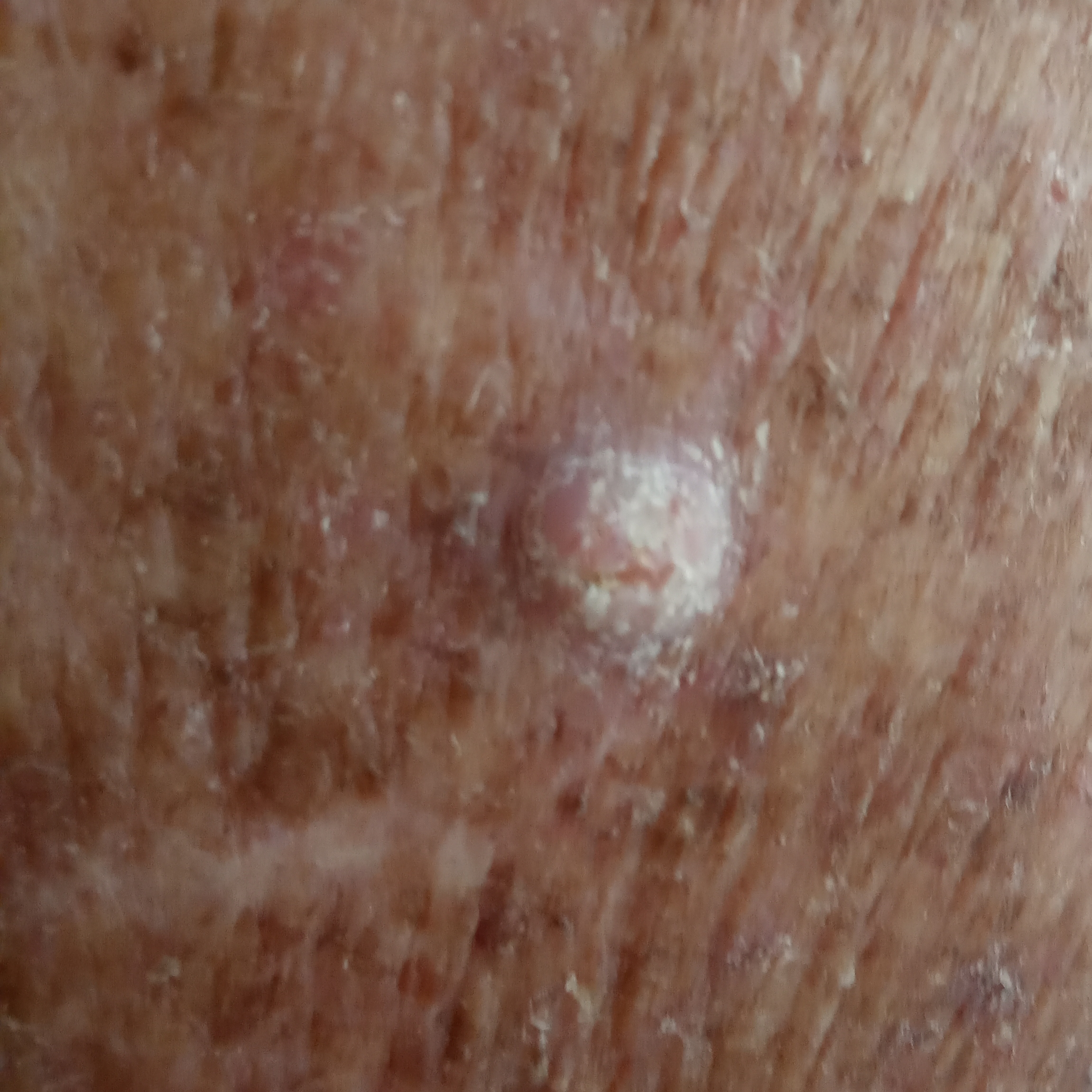A male subject 69 years old.
A clinical photograph of a skin lesion.
Recorded as Fitzpatrick III.
History notes tobacco use, prior malignancy (patient or family), and alcohol use.
The lesion involves an arm.
The lesion is roughly 7 by 7 mm.
By the patient's account, the lesion is elevated, has changed, has grown, and itches.
Biopsy-confirmed as a squamous cell carcinoma.